A dermoscopic image of a skin lesion.
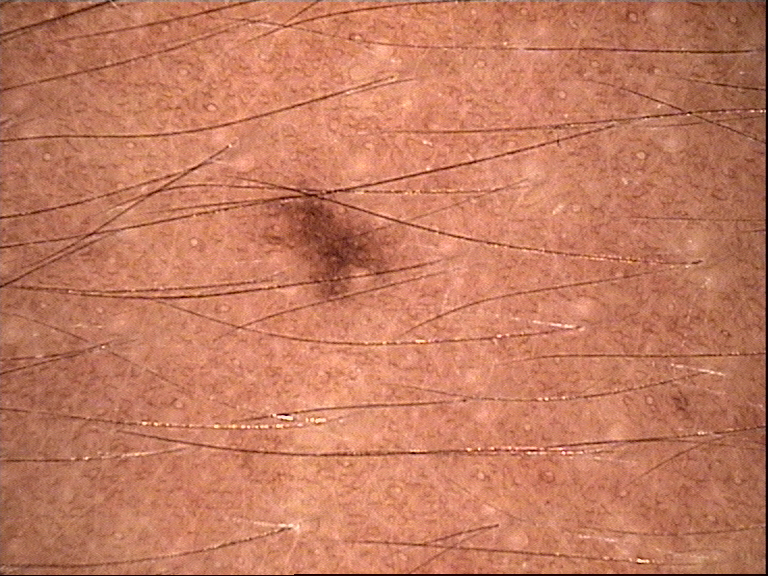Q: How is the lesion classified?
A: banal
Q: What is this lesion?
A: junctional nevus (expert consensus)